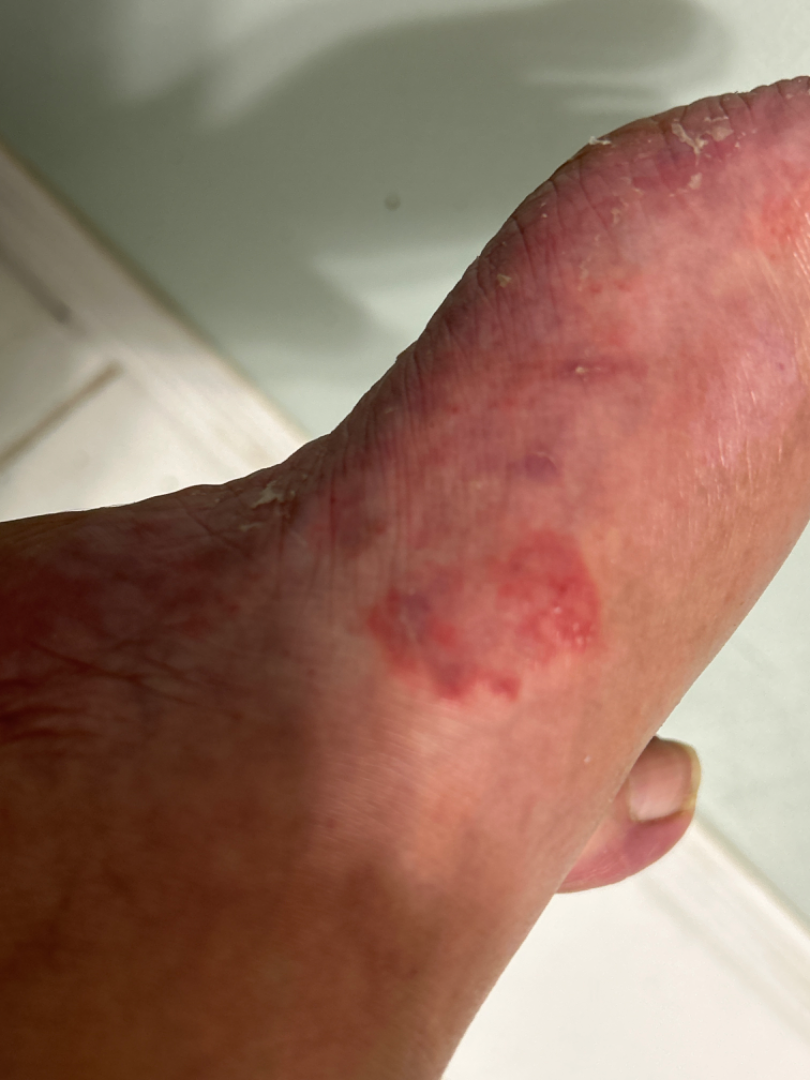  shot_type: close-up
  differential:
    leading:
      - Granuloma annulare